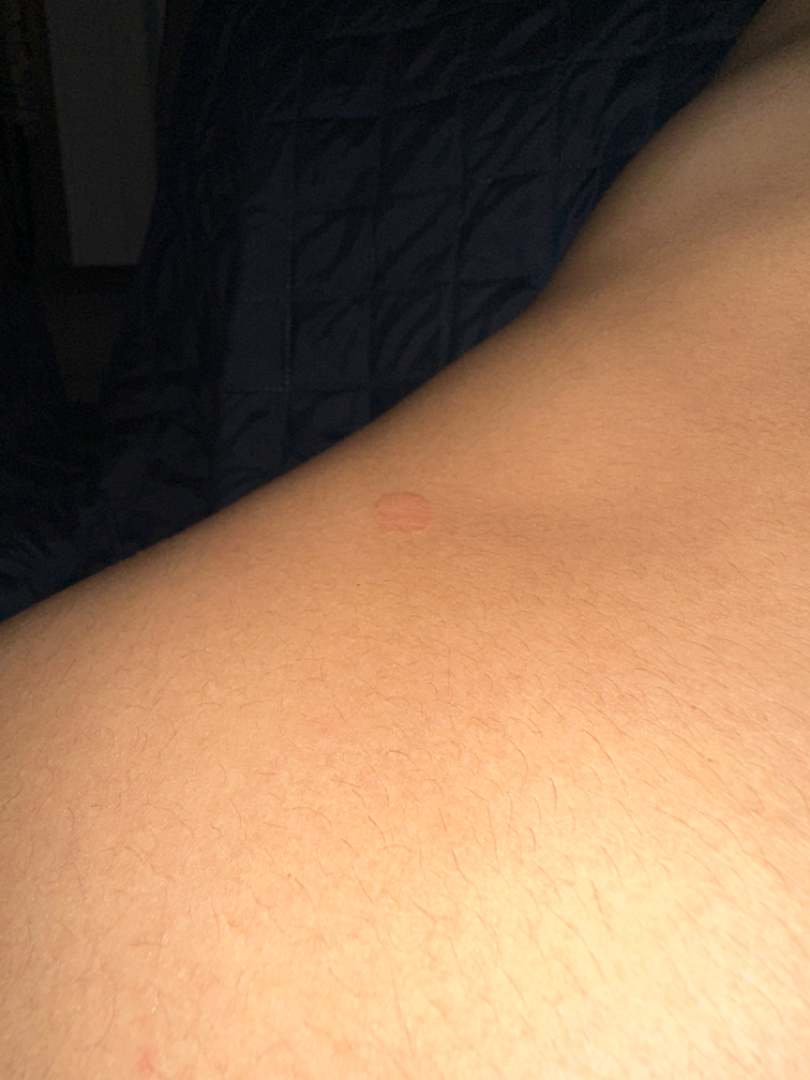The case was indeterminate on photographic review.
Fitzpatrick skin type III.
The photo was captured at an angle.